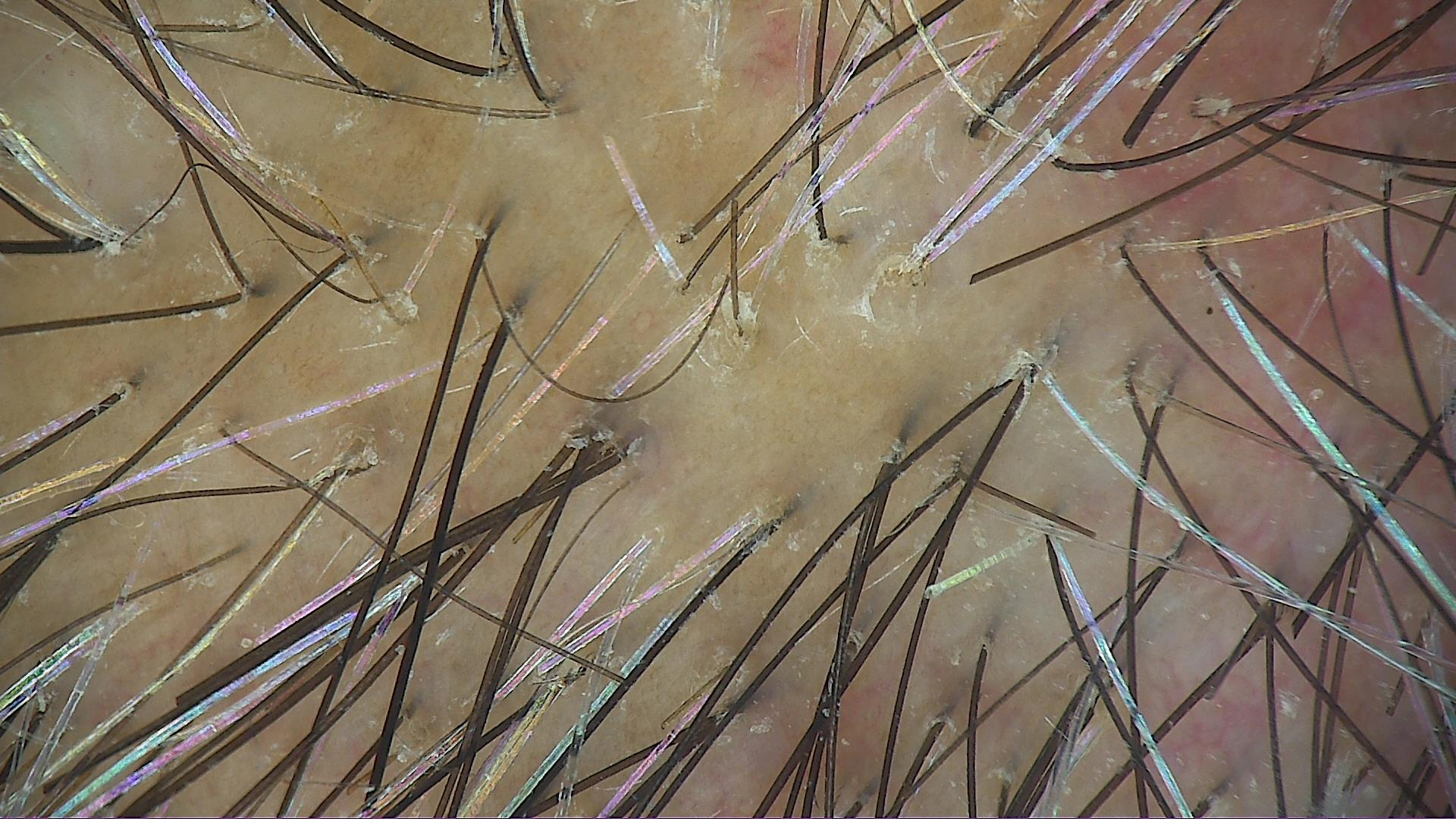Case: Dermoscopy of a skin lesion. The morphology is that of a fibro-histiocytic lesion. Impression: Consistent with a dermatofibroma.